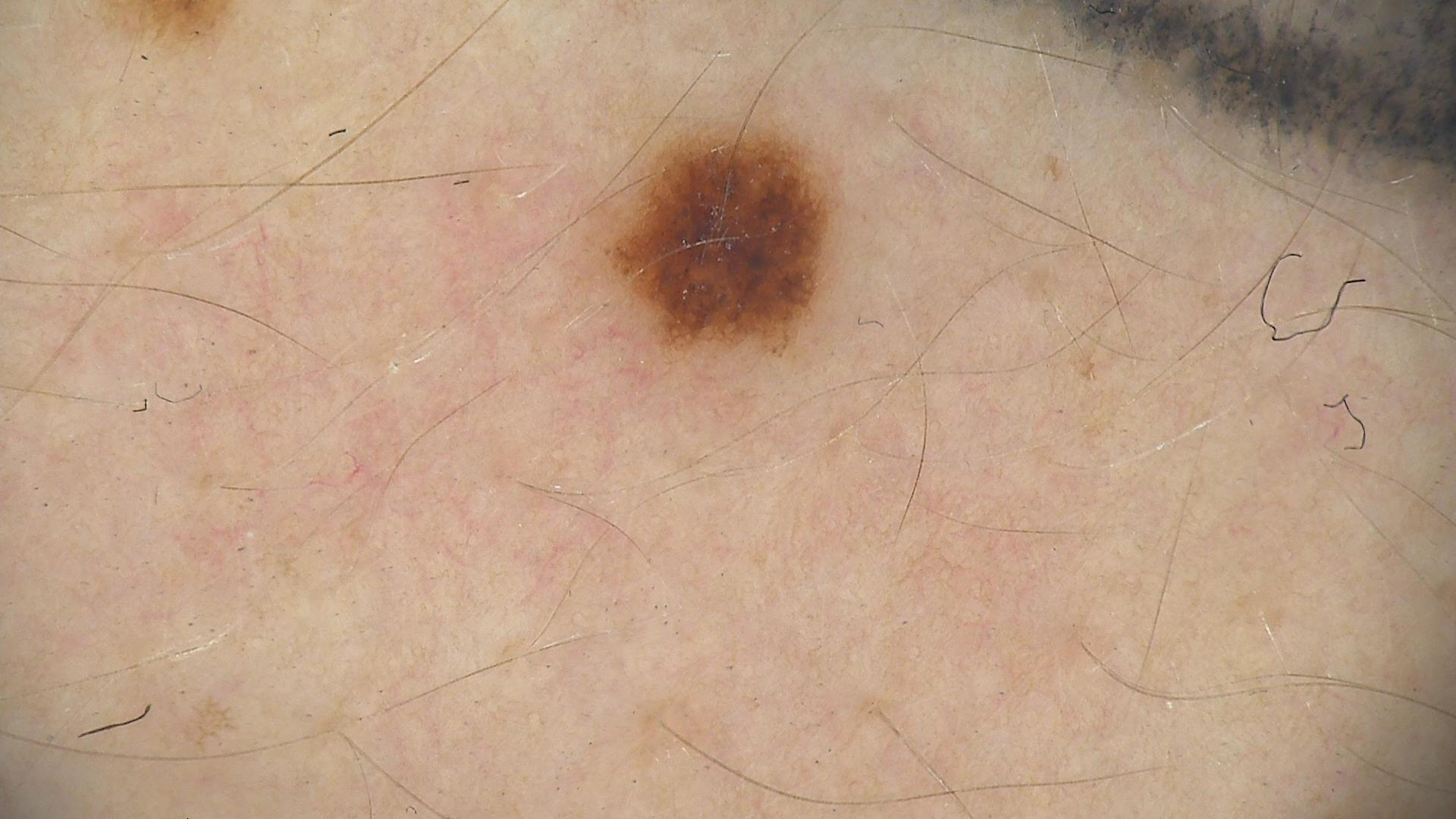The diagnosis was a dysplastic junctional nevus.